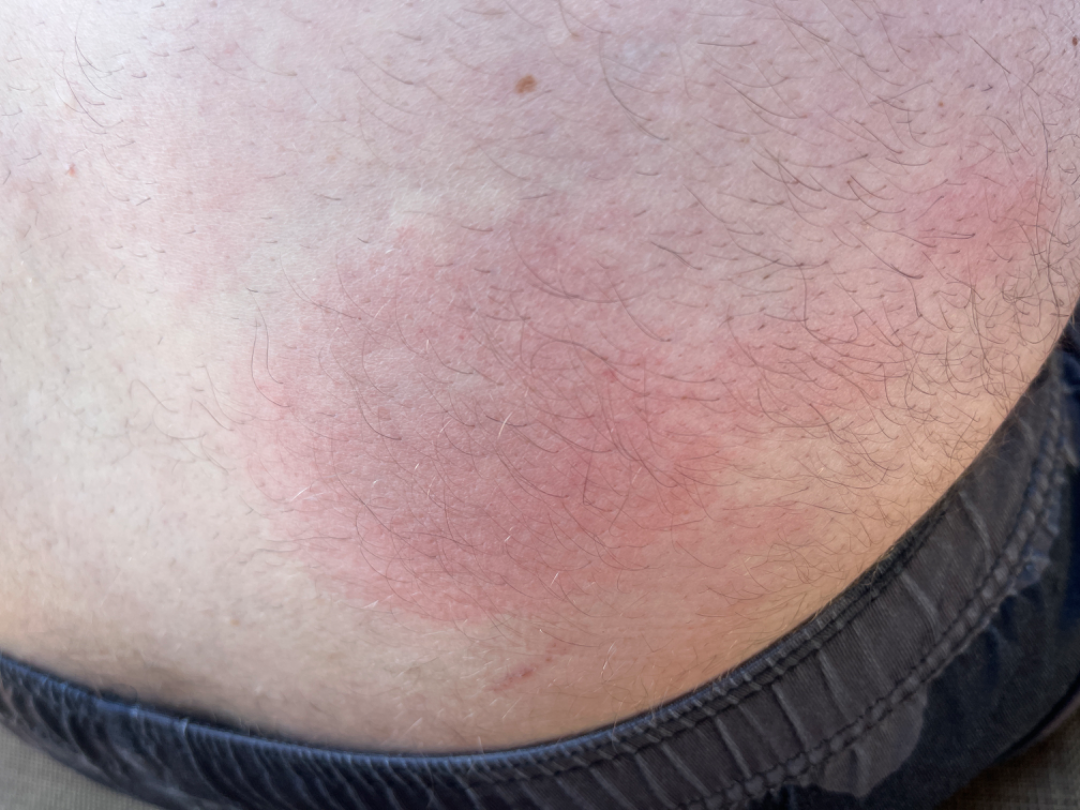The reviewer was unable to grade this case for skin condition. Texture is reported as flat. Located on the leg, front of the torso, back of the torso and arm. Reported lesion symptoms include enlargement and bothersome appearance. The photograph is a close-up of the affected area. Fitzpatrick skin type III. Self-categorized by the patient as a rash. Reported duration is one to four weeks. The contributor notes associated fatigue, chills and joint pain.